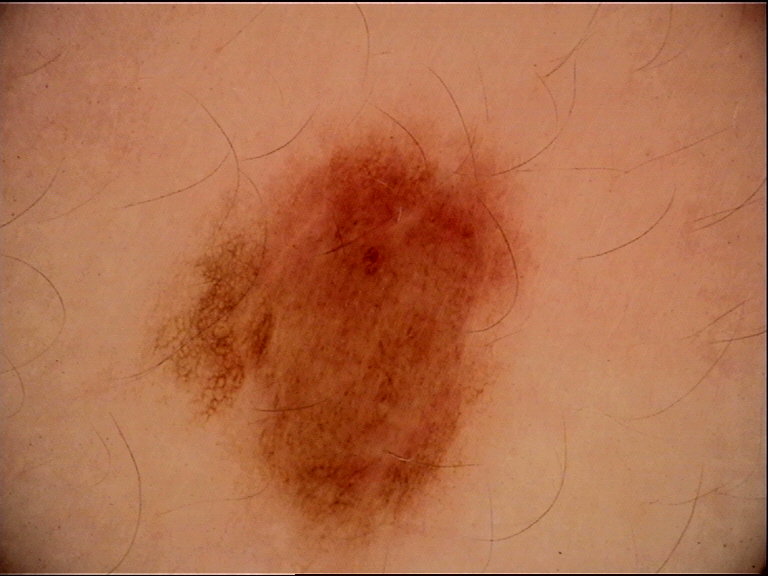Case:
A dermoscopic photograph of a skin lesion.
Impression:
The diagnostic label was a benign lesion — a dysplastic junctional nevus.